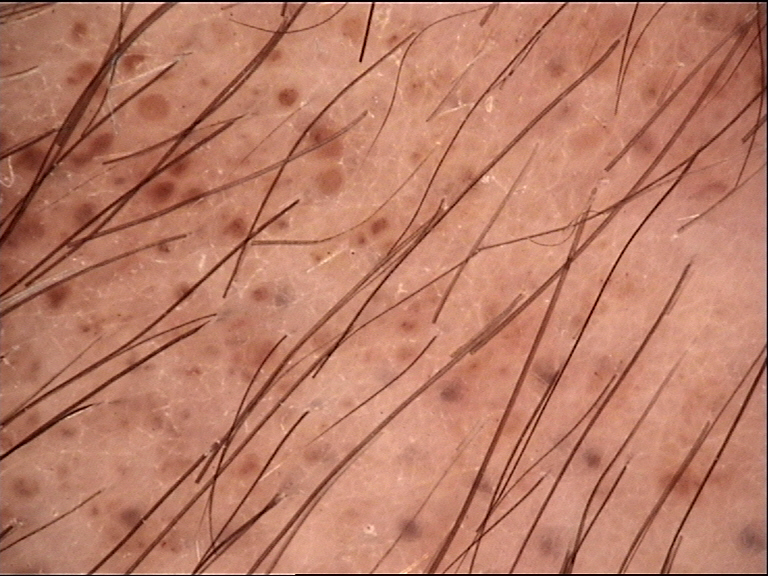Q: What is the imaging modality?
A: dermatoscopy
Q: How is the lesion classified?
A: banal
Q: What is this lesion?
A: congenital compound nevus (expert consensus)